A skin lesion imaged with a dermatoscope.
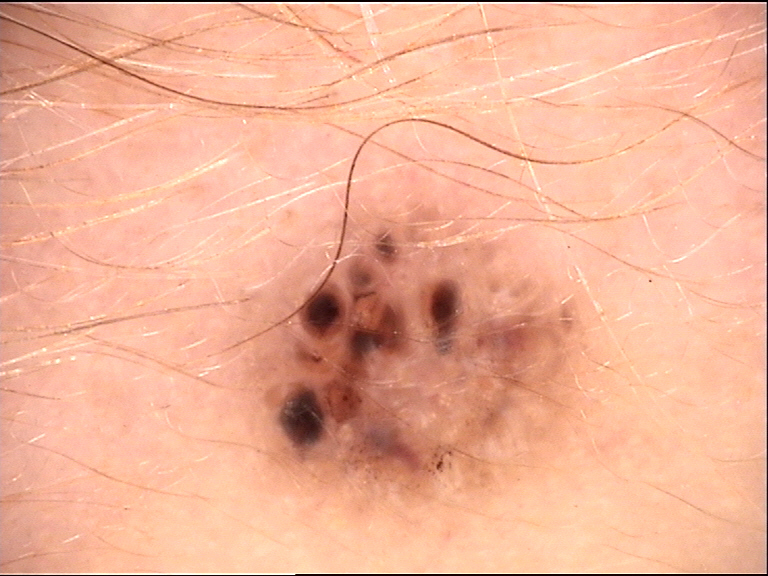This is a keratinocytic lesion.
Biopsy-confirmed as a malignancy — a basal cell carcinoma.